Dermoscopy of a skin lesion:
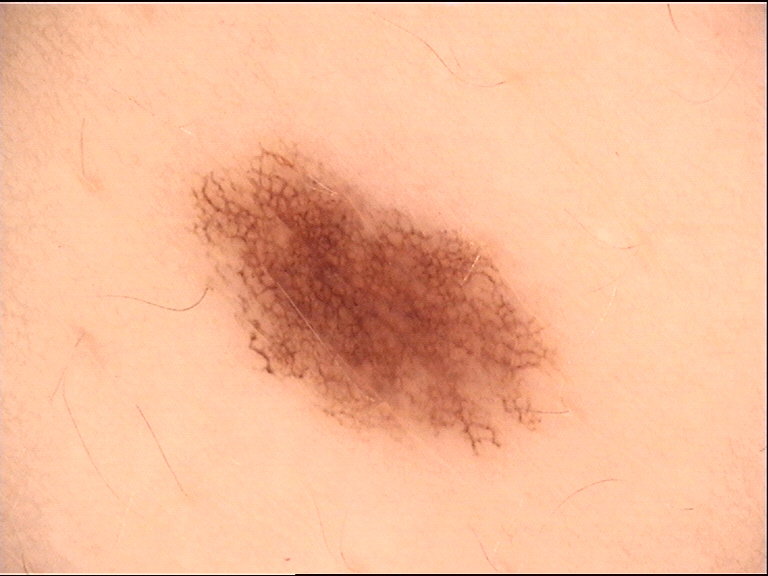The architecture is that of a banal lesion. Diagnosed as a junctional nevus.